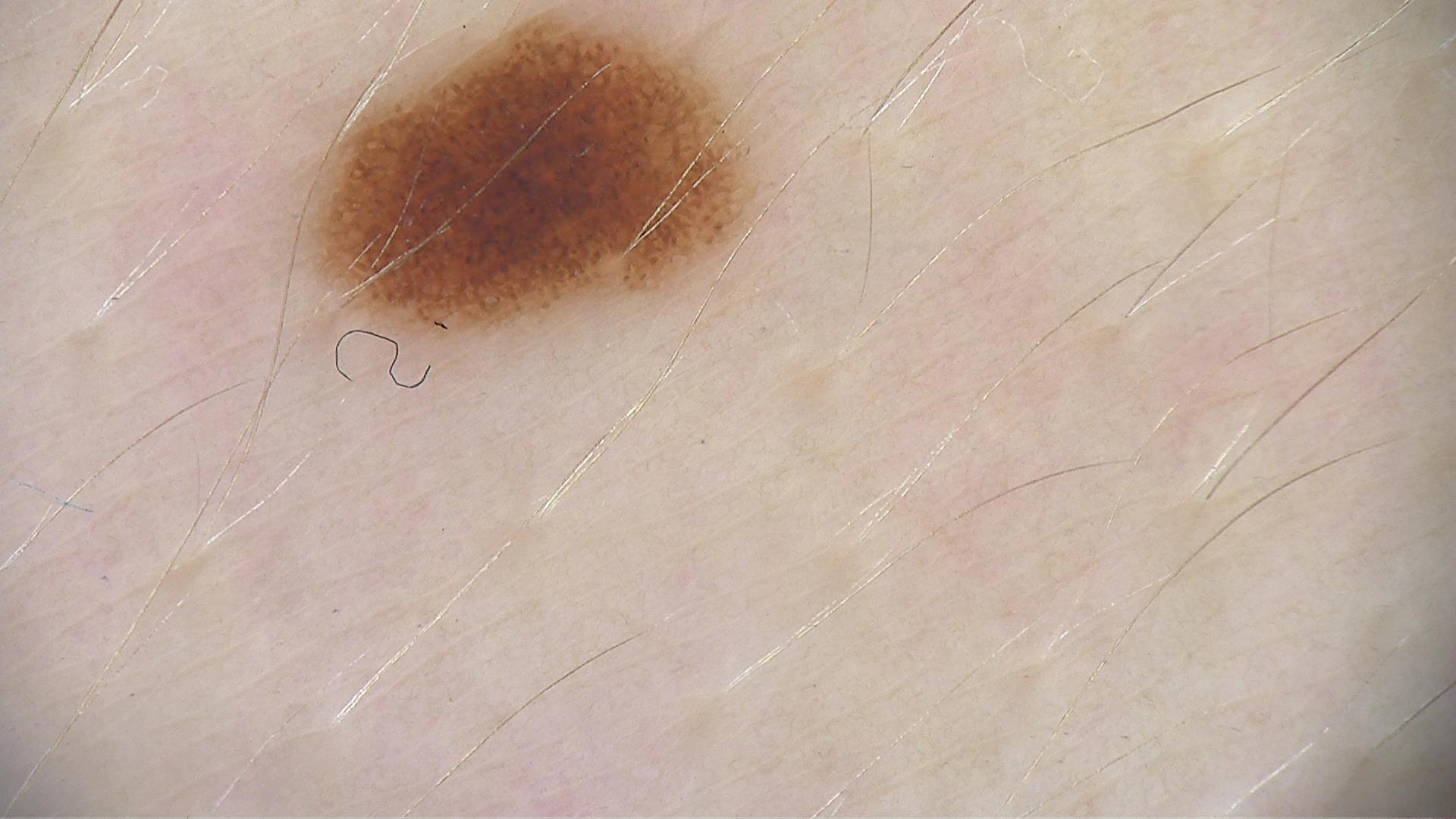image type = dermatoscopy | class = dysplastic junctional nevus (expert consensus).